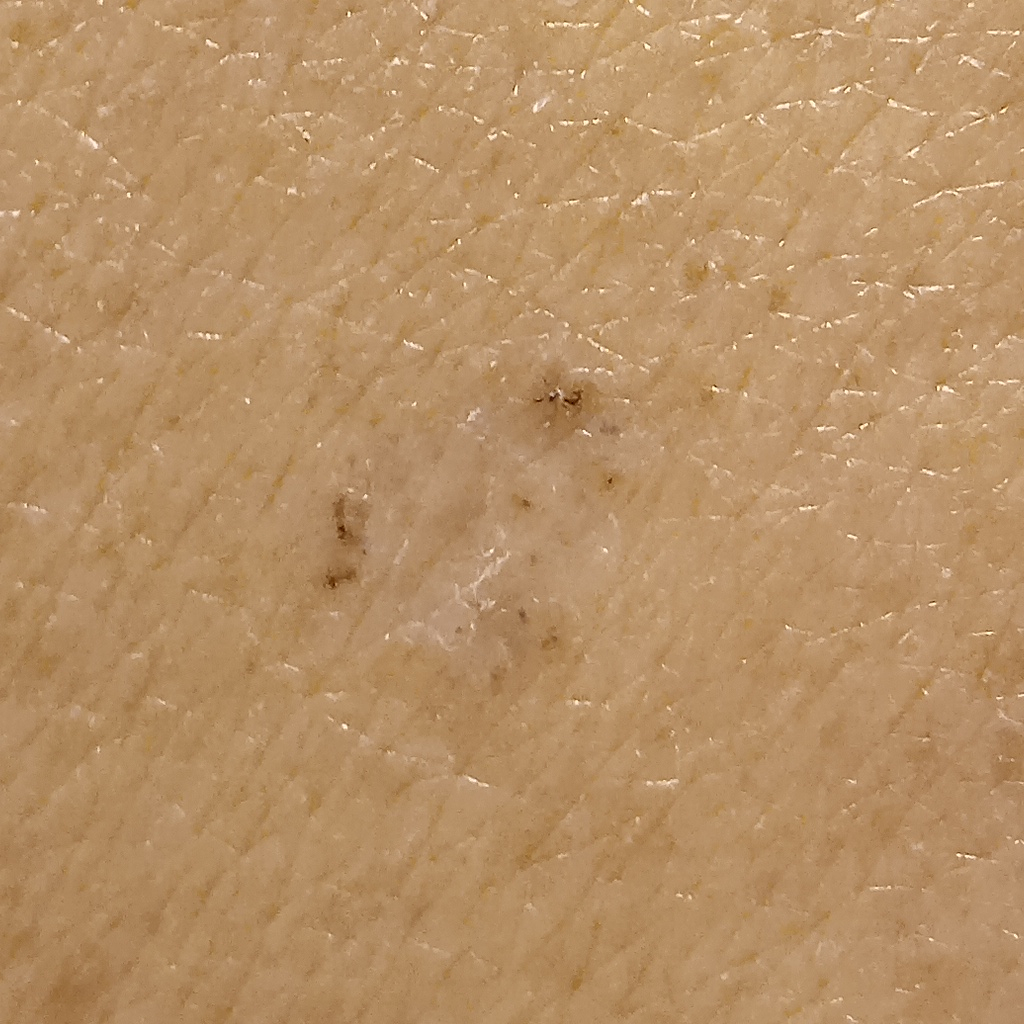Referred with a clinical suspicion of basal cell carcinoma. By self-report, a personal history of skin cancer, a personal history of cancer, no family history of skin cancer, and no sunbed use. Few moles overall by the patient's own estimate. The lesion involves the back. Measuring roughly 7.8 mm. Dermatologist review favored a basal cell carcinoma.